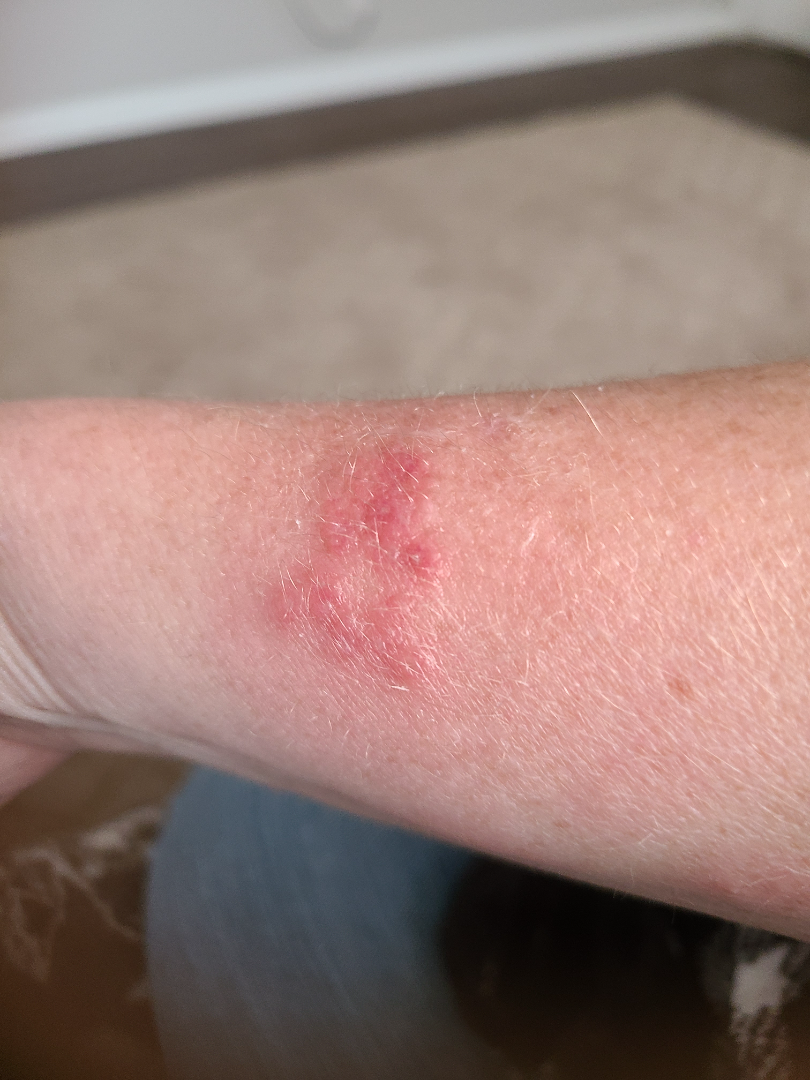  patient: female, age 40–49
  shot_type: close-up
  body_site: arm
  differential:
    leading:
      - Herpes Simplex